A skin lesion imaged with a dermatoscope.
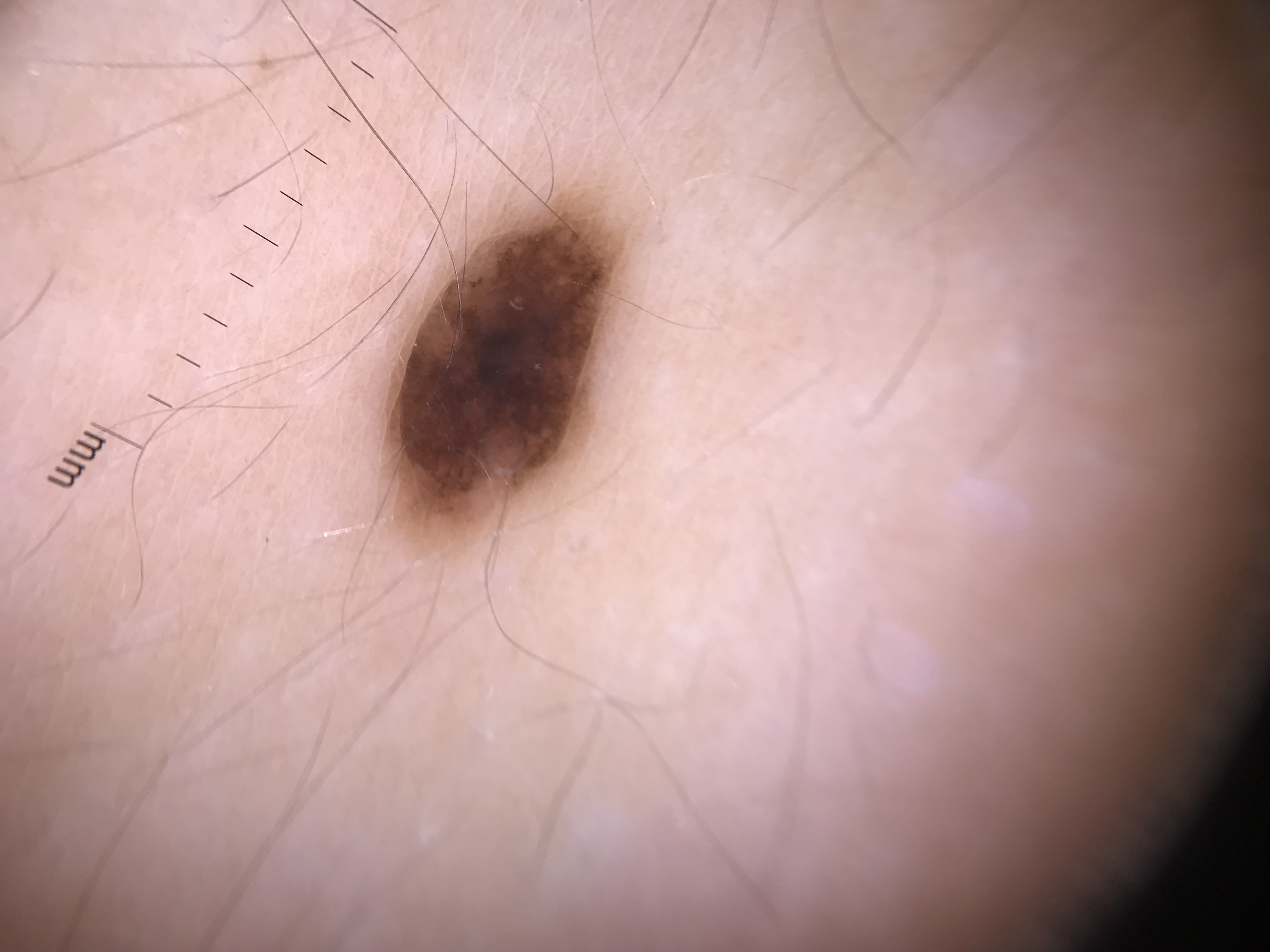Q: How is the lesion classified?
A: banal
Q: What is this lesion?
A: compound nevus (expert consensus)